A dermoscopy image of a single skin lesion.
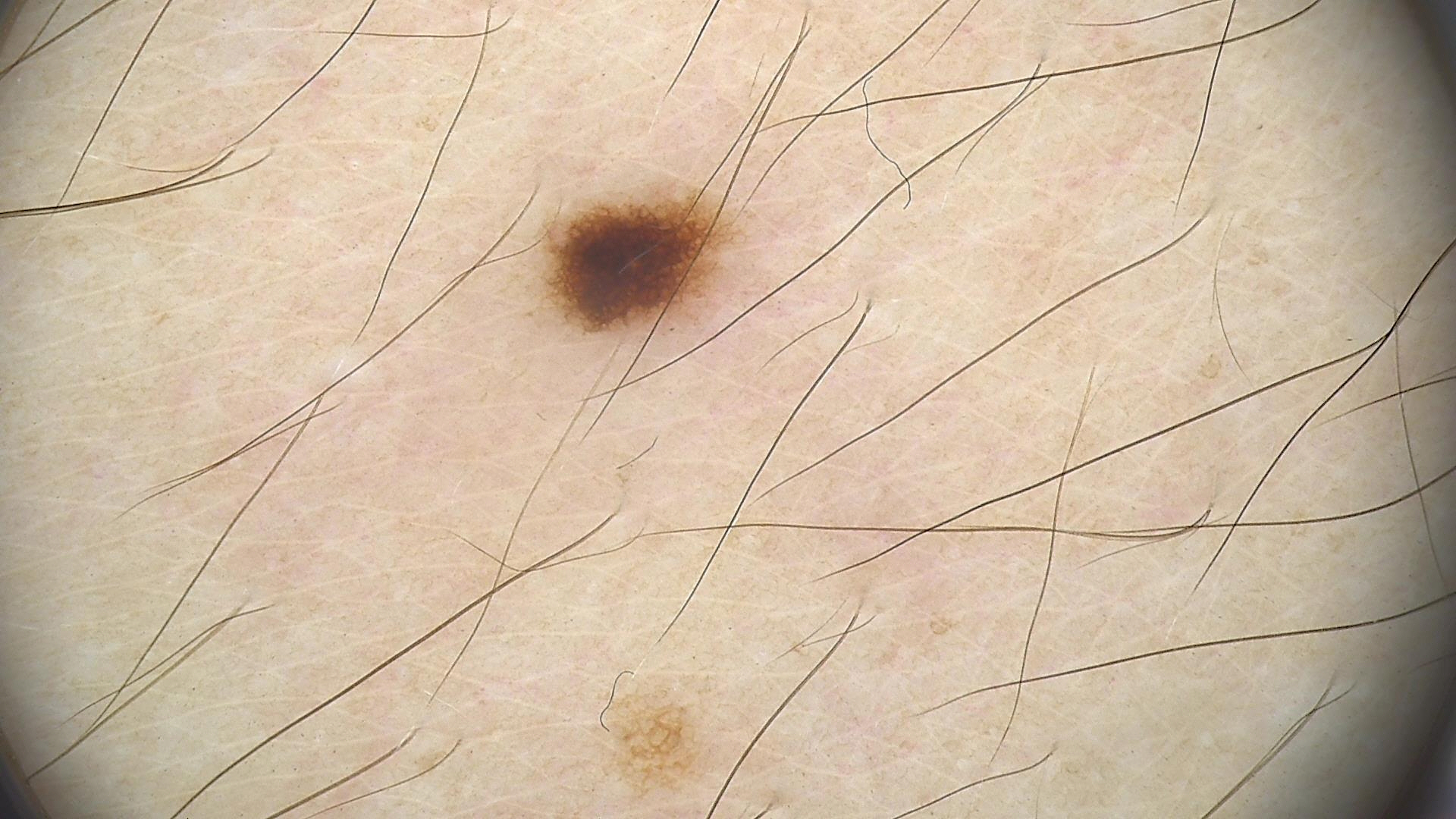<case>
  <diagnosis>
    <name>dysplastic junctional nevus</name>
    <code>jd</code>
    <malignancy>benign</malignancy>
    <super_class>melanocytic</super_class>
    <confirmation>expert consensus</confirmation>
  </diagnosis>
</case>